A skin lesion imaged with a dermatoscope:
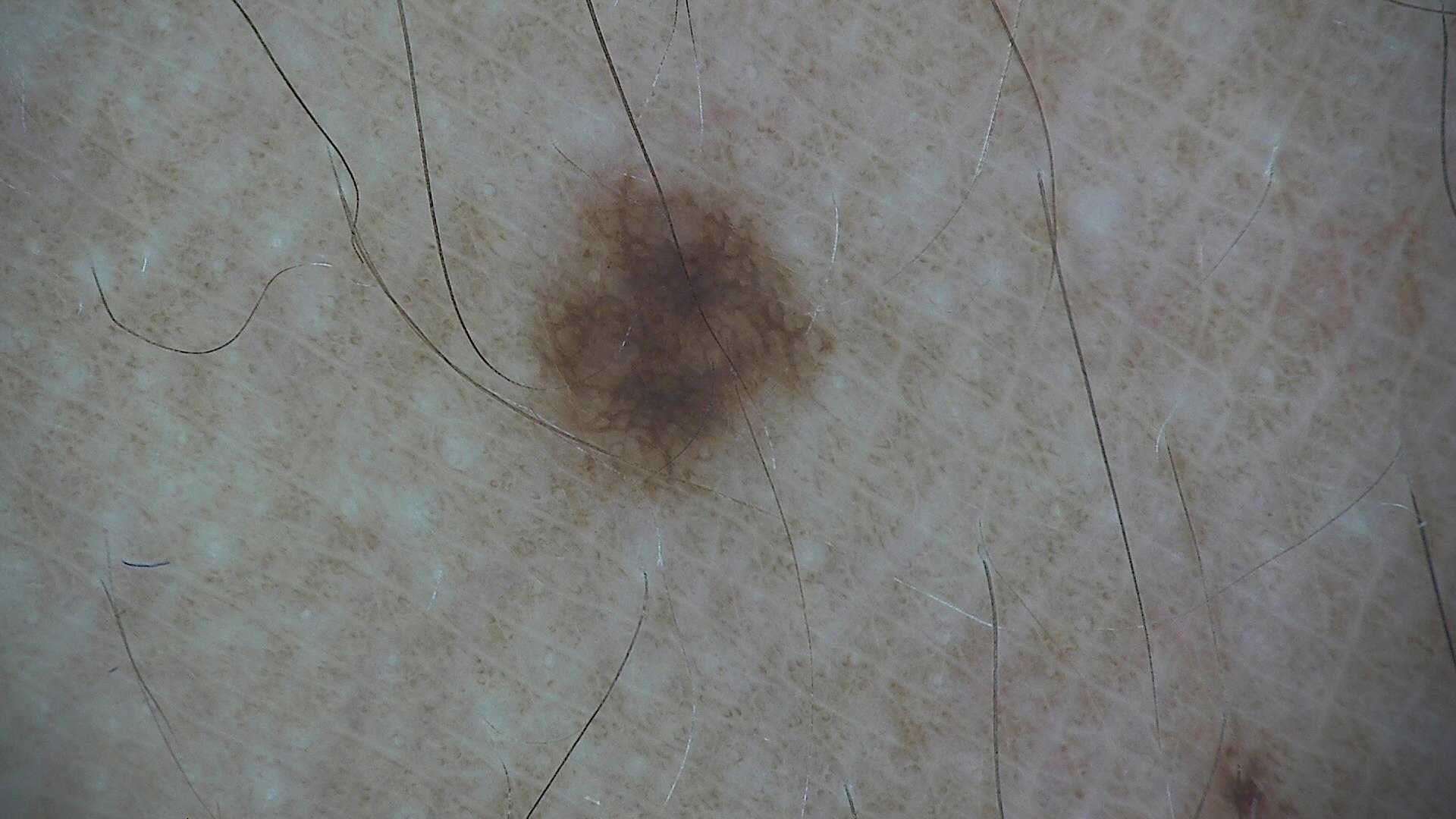Labeled as a benign lesion — a dysplastic junctional nevus.